The photograph is a close-up of the affected area:
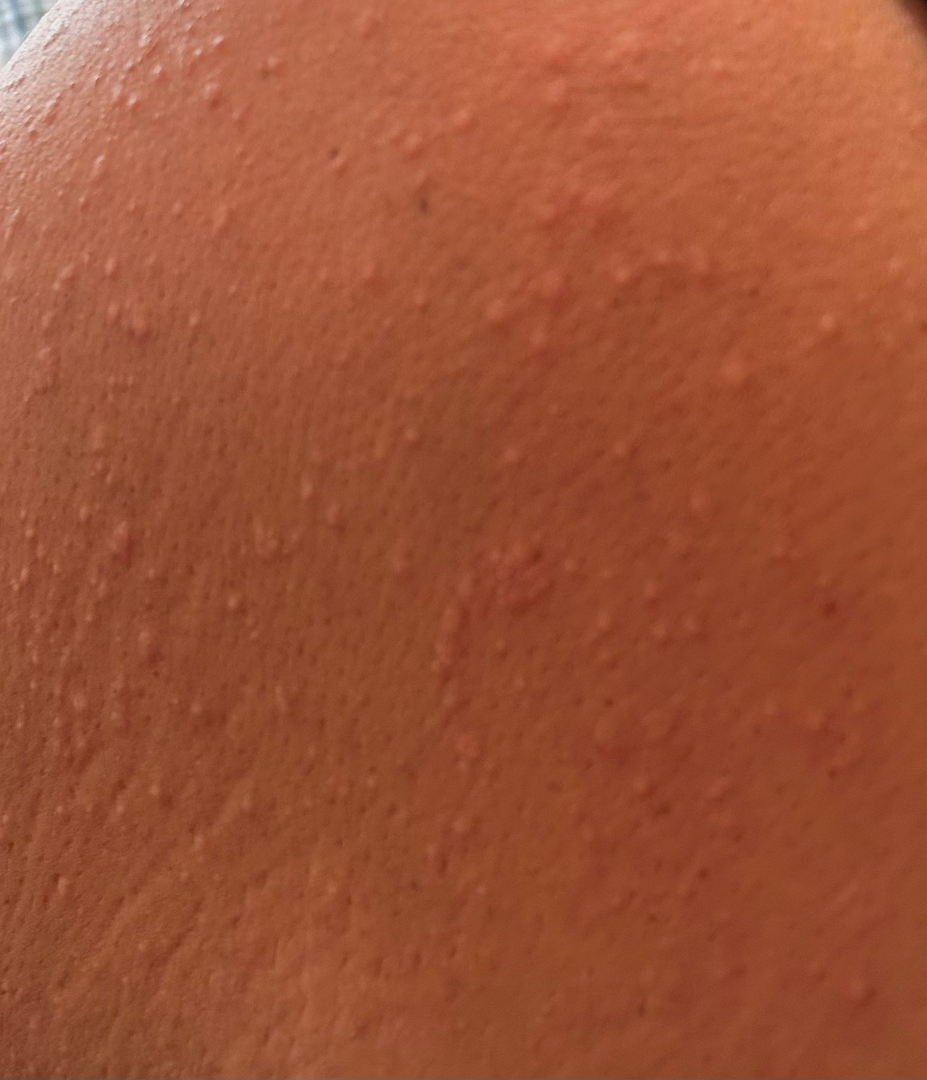assessment — not assessable